A dermatoscopic image of a skin lesion. A female patient, aged approximately 10 — 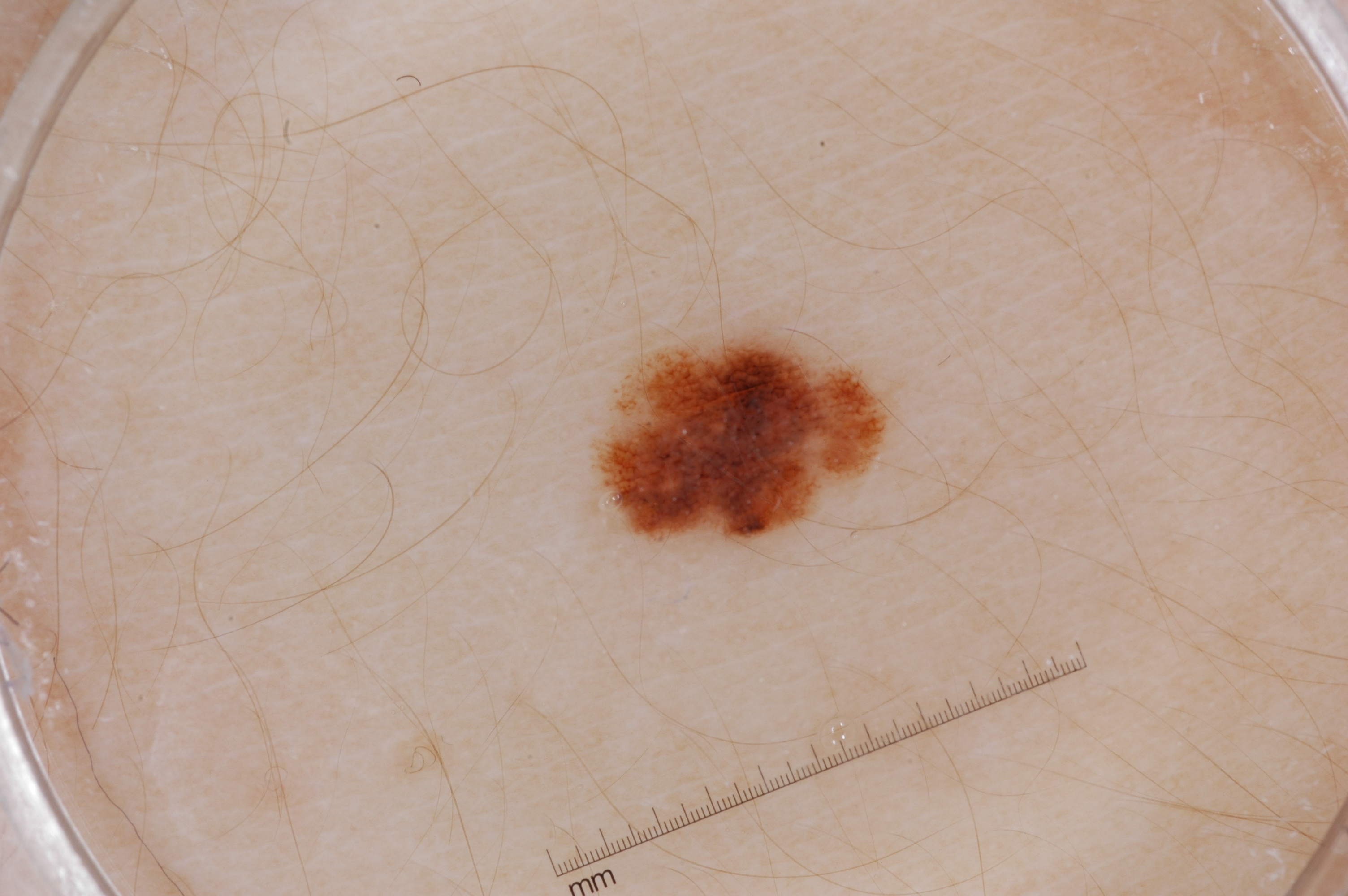Q: Where is the lesion in the image?
A: bbox=[578, 318, 894, 555]
Q: What dermoscopic features are present?
A: pigment network
Q: What is the diagnosis?
A: a melanocytic nevus, a benign skin lesion